A dermatoscopic image of a skin lesion.
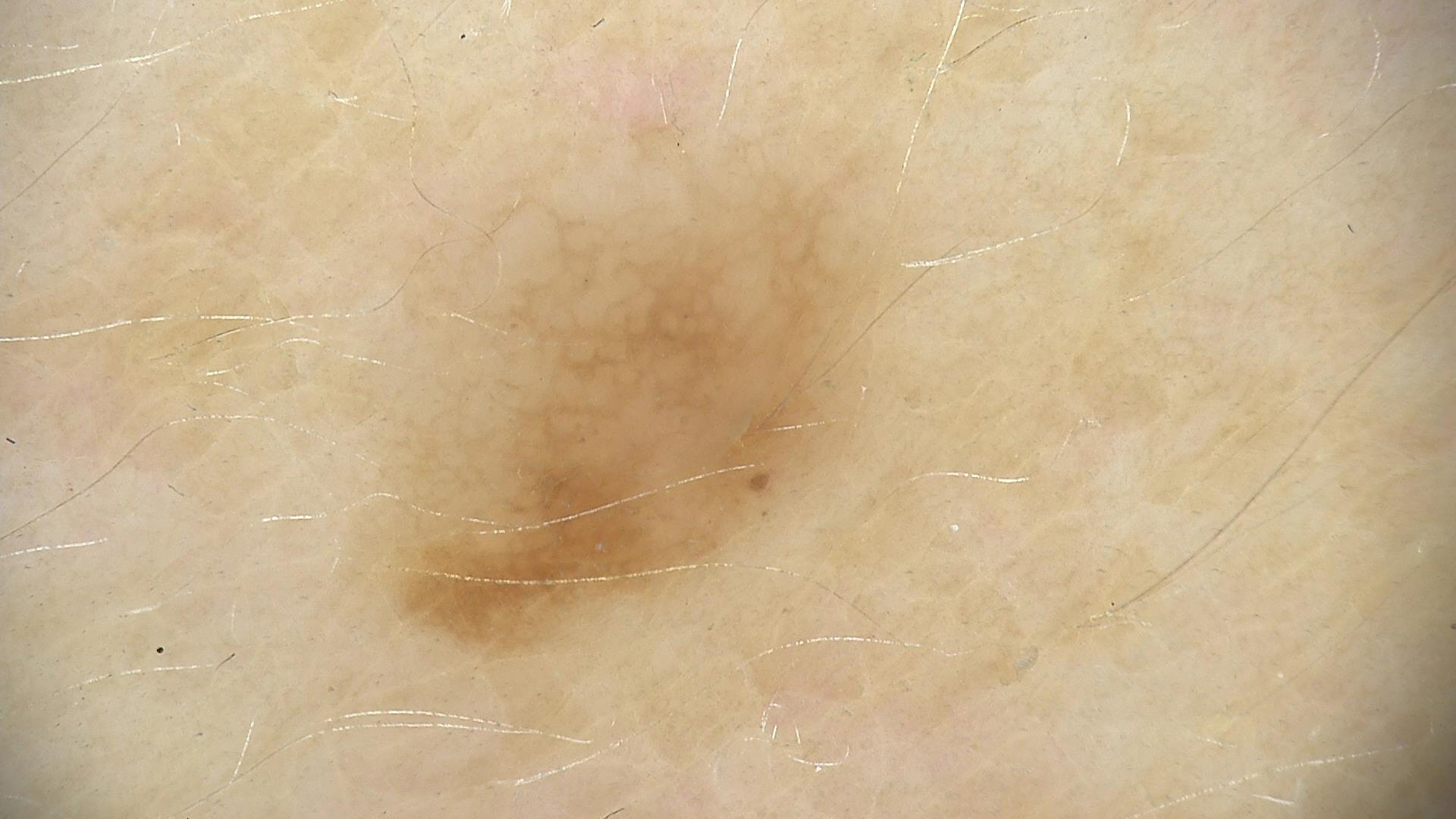class — dysplastic junctional nevus (expert consensus).